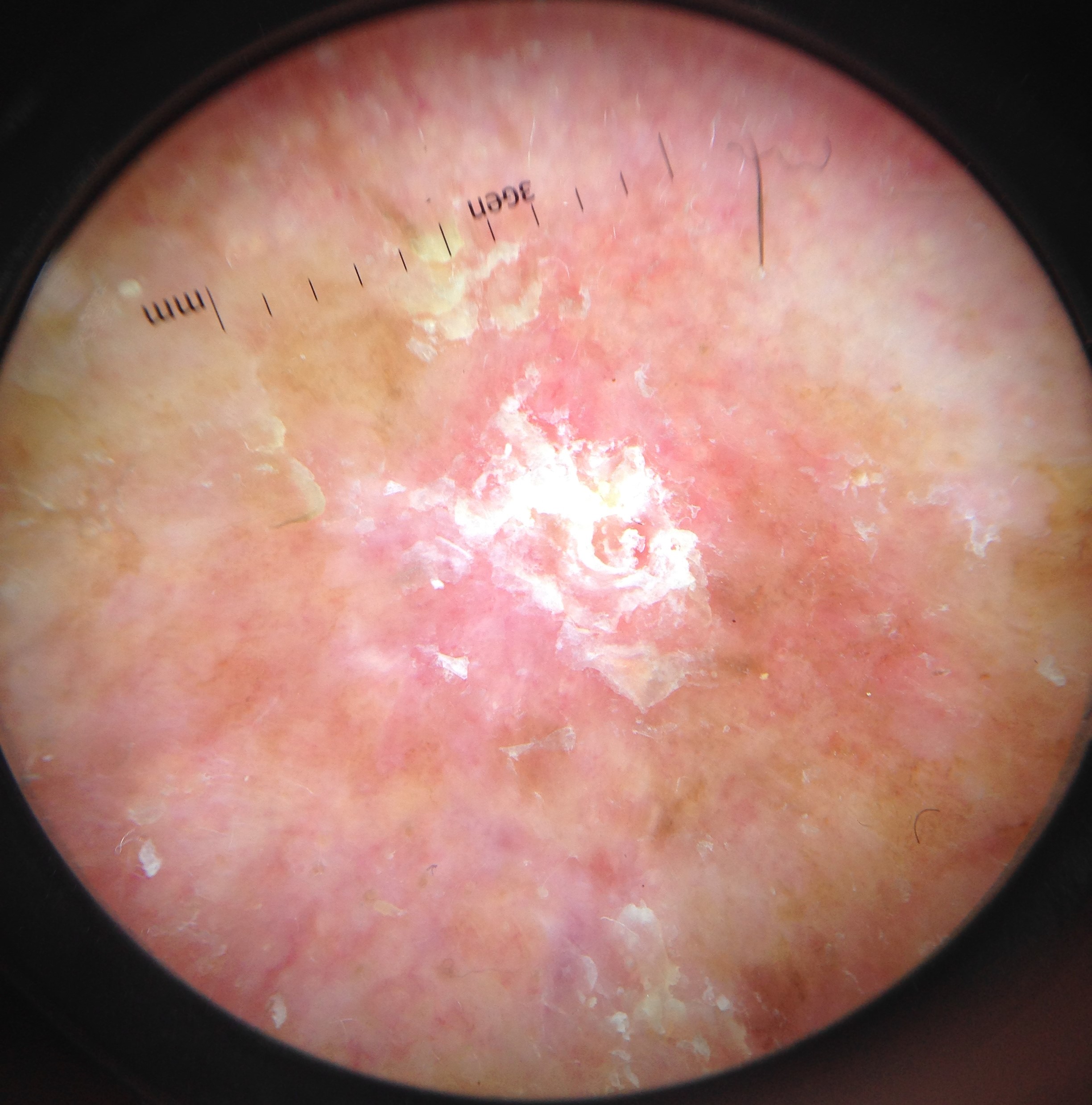The biopsy diagnosis was a squamous cell carcinoma.